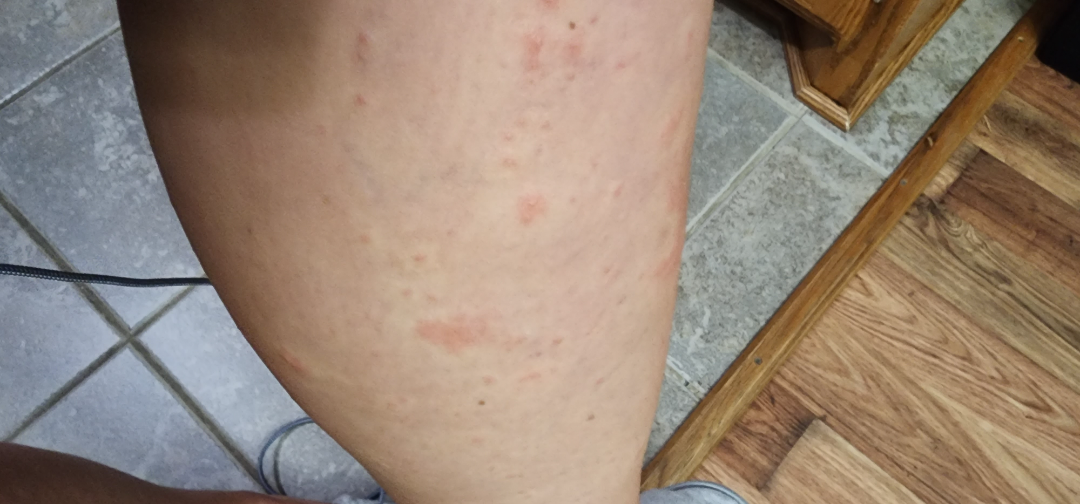The differential includes Acute vesicular dermatitis and Allergic Contact Dermatitis, with no clear leading consideration.